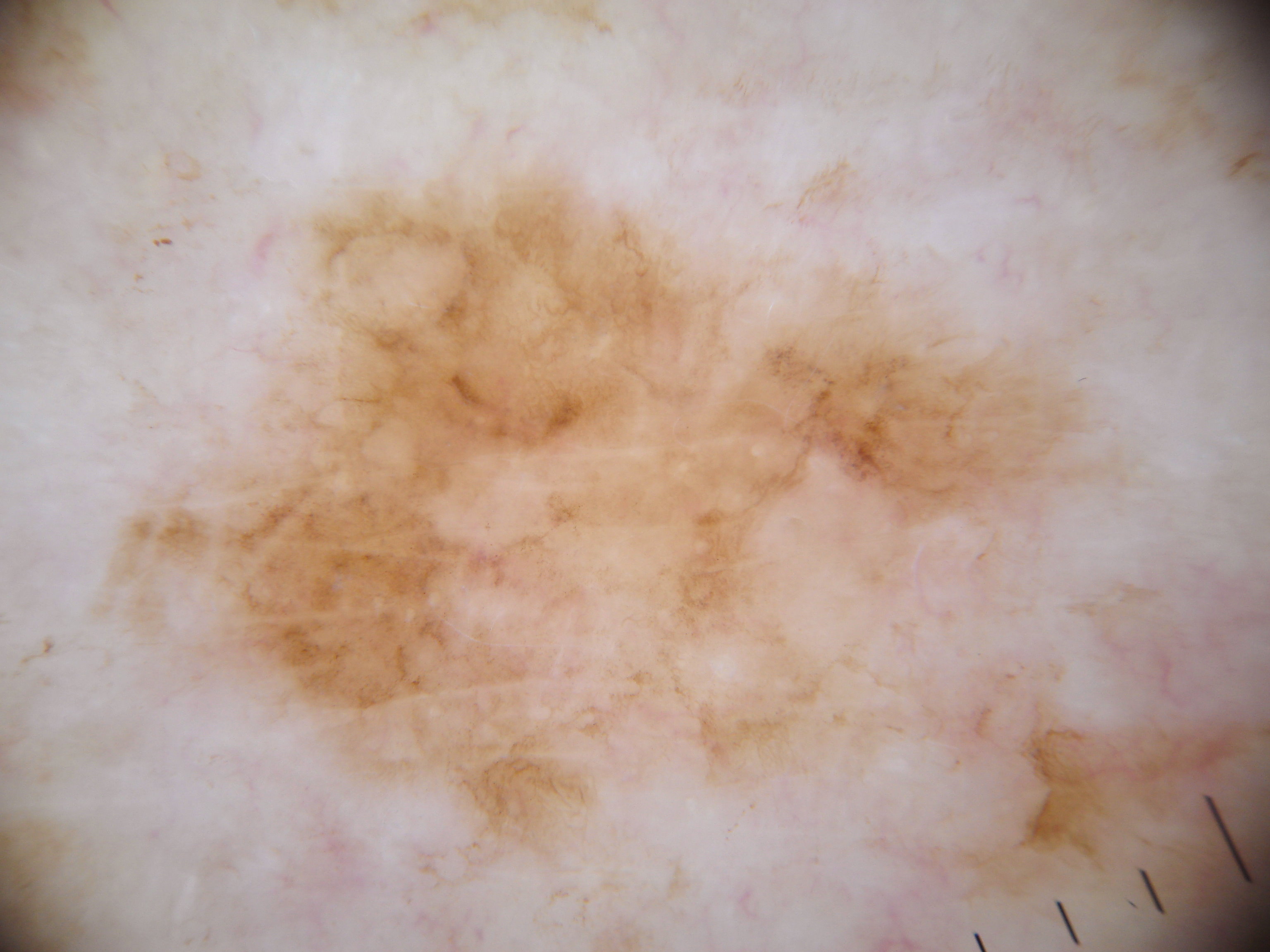Case summary:
* imaging · dermoscopic image
* location · bbox=[95, 158, 1235, 908]
* absent dermoscopic findings · pigment network, negative network, globules, streaks, and milia-like cysts
* impression · a melanoma